The lesion involves the head or neck. Close-up view.
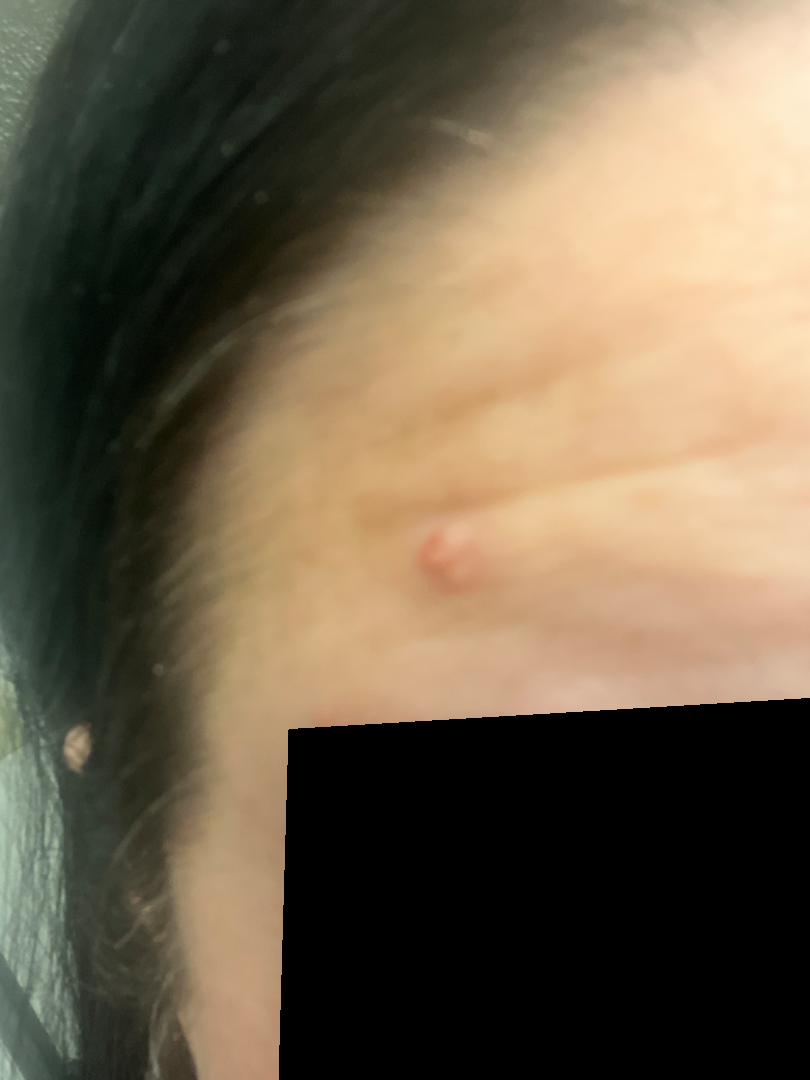Impression:
The reviewer was unable to grade this case for skin condition.
History:
The lesion is associated with enlargement. Present for three to twelve months. The lesion is described as rough or flaky and raised or bumpy. The patient considered this a growth or mole. No associated systemic symptoms reported.